Located on the palm · this image was taken at a distance · male patient, age 60–69 — 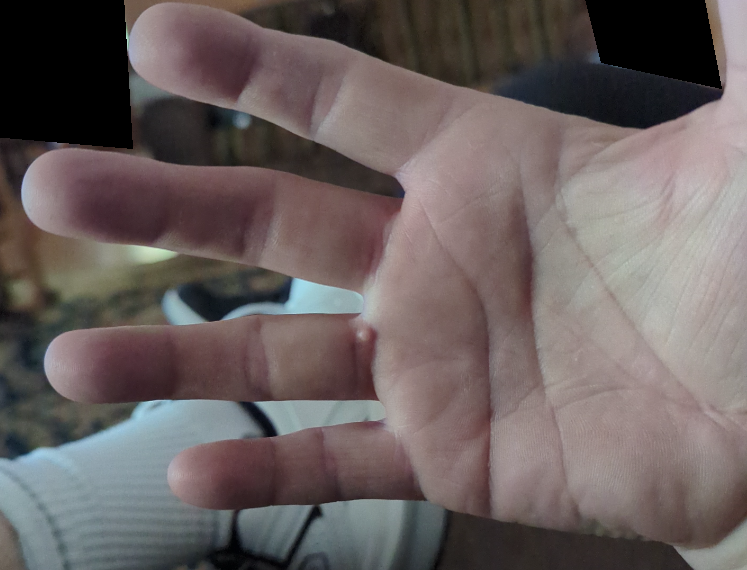differential:
  leading:
    - Melanocytic Nevus
  considered:
    - Verruca vulgaris
  unlikely:
    - Cyst
    - Adnexal neoplasm
    - Acquired digital fibrokeratoma